A dermoscopic view of a skin lesion; a male patient roughly 60 years of age:
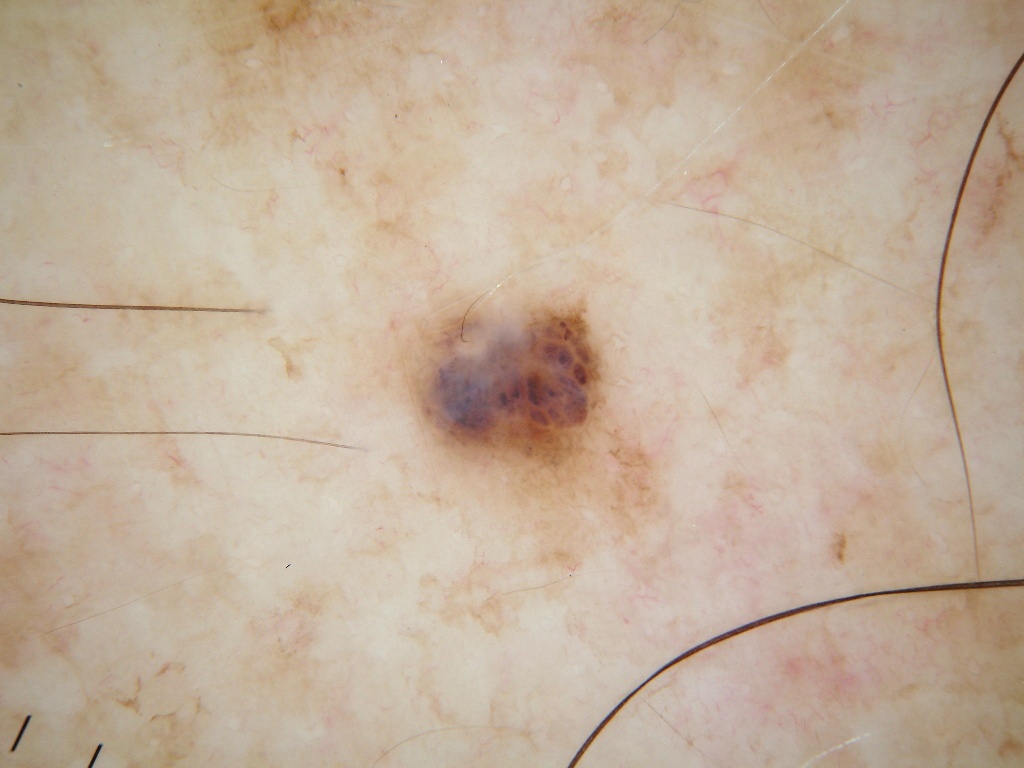Image and clinical context:
Dermoscopic examination shows no globules, streaks, milia-like cysts, negative network, or pigment network. A small lesion within a wider field of skin. The lesion's extent is [414, 307, 603, 472].
Conclusion:
Diagnosed as a melanocytic nevus.